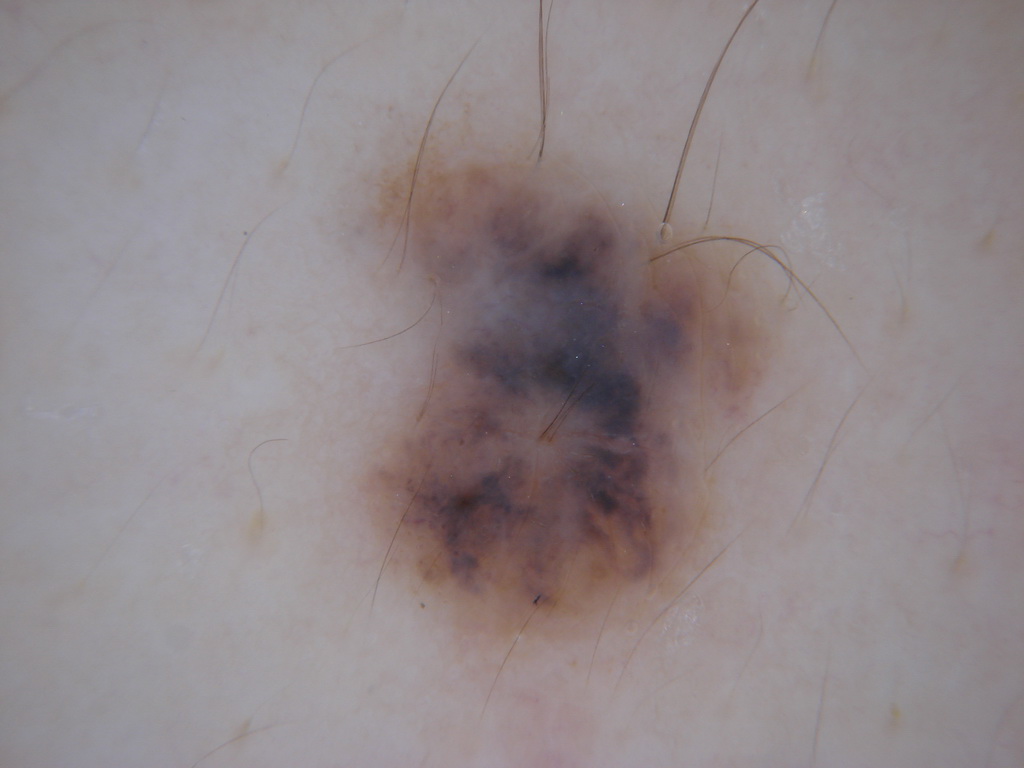A dermoscopy image of a single skin lesion. A female subject, roughly 25 years of age. On dermoscopy, the lesion shows no pigment network, globules, streaks, negative network, or milia-like cysts. As (left, top, right, bottom), the lesion is located at 331, 104, 813, 668. Consistent with a melanocytic nevus, a benign lesion.